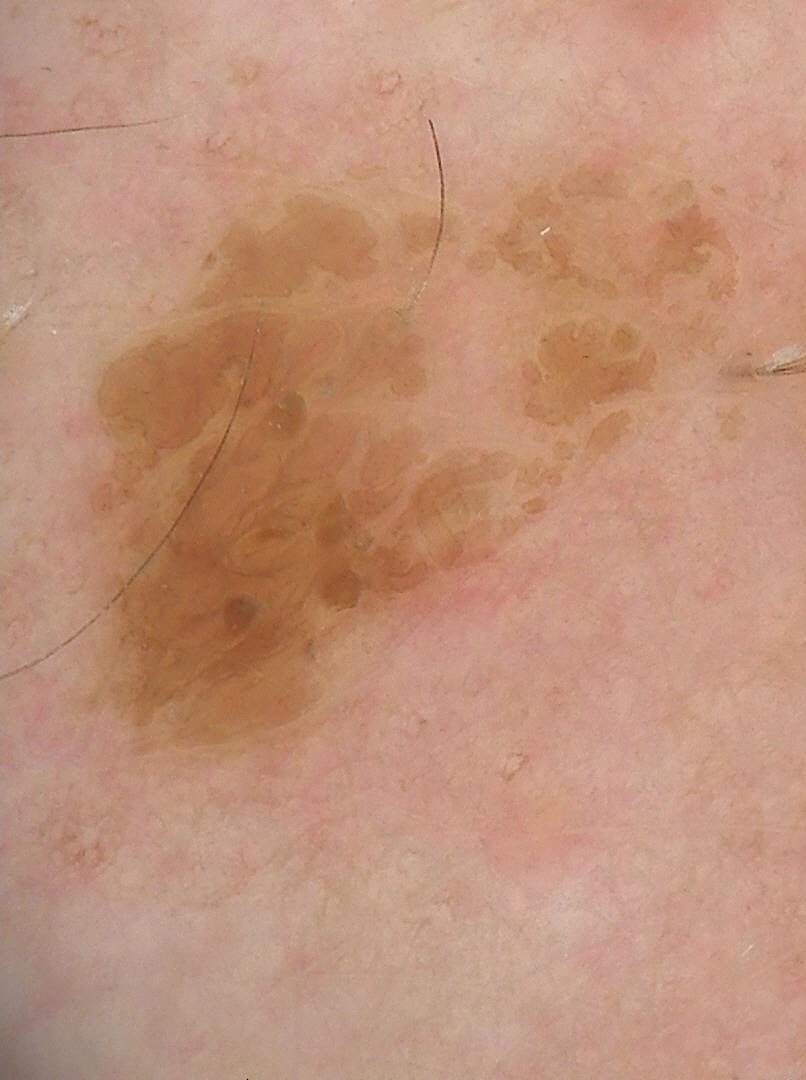Summary:
A dermoscopy image of a single skin lesion.
Impression:
Consistent with a keratinocytic lesion — a seborrheic keratosis.